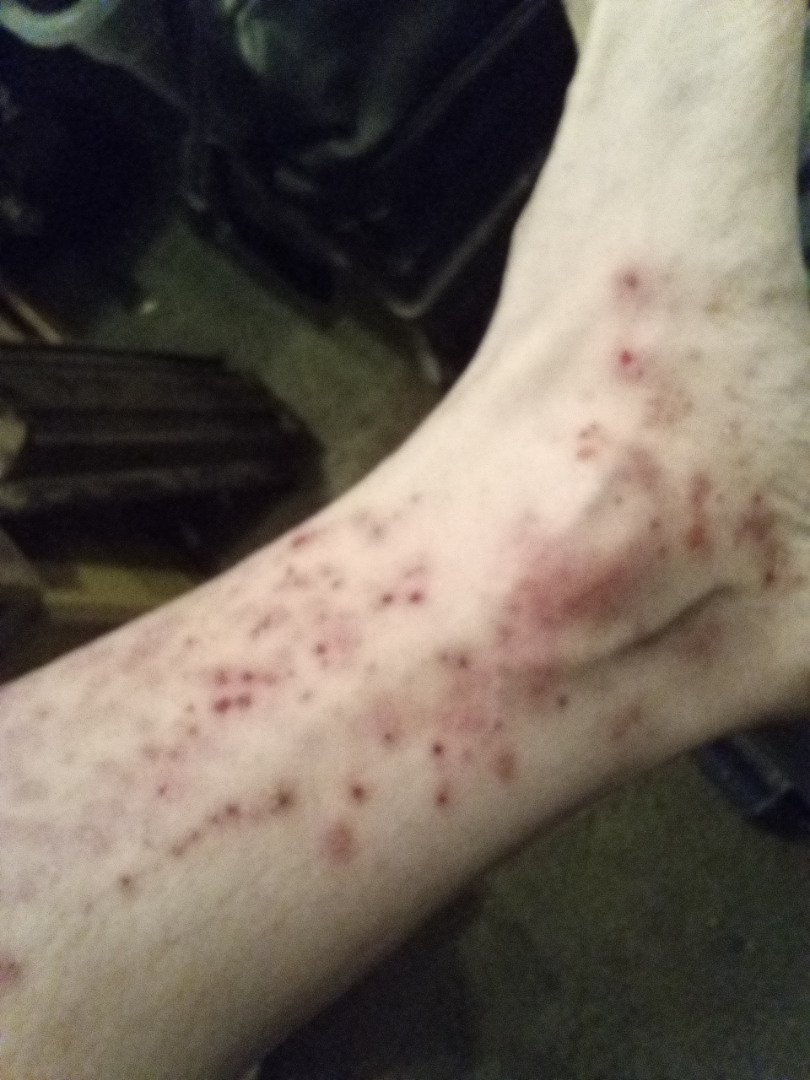The arm and top or side of the foot are involved. The contributor notes the condition has been present for three to twelve months. Skin tone: Fitzpatrick II; lay reviewers estimated a MST of 2. Symptoms reported: itching, enlargement, pain and bleeding. This is a close-up image. The contributor is male. On teledermatology review, the differential, in no particular order, includes Insect Bite and Eczema.